The photo was captured at a distance. The arm is involved. The subject is a female aged 40–49 — 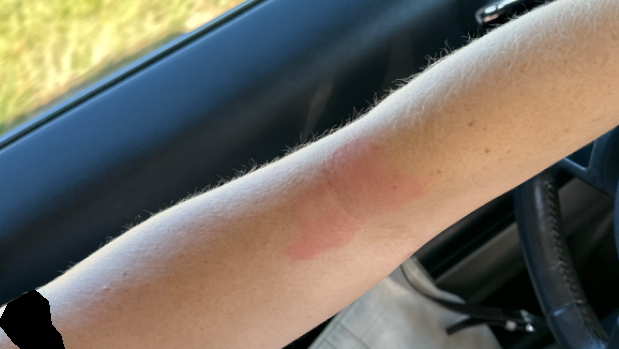patient describes the issue as=a rash
other reported symptoms=joint pain
patient-reported symptoms=bothersome appearance, darkening, itching, enlargement and pain
present for=more than one year
diagnostic considerations=most consistent with Eczema